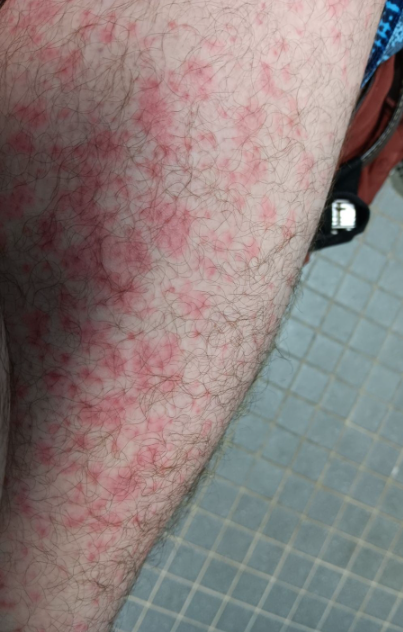assessment = unable to determine
location = palm, leg, front of the torso, back of the torso, top or side of the foot and arm
skin tone = Fitzpatrick II; lay reviewers estimated a Monk Skin Tone of 2
photo taken = close-up